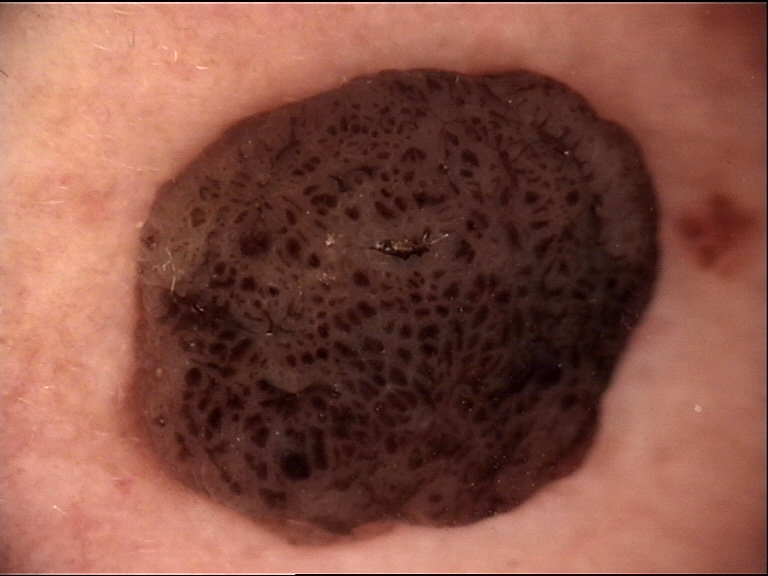A dermoscopic photograph of a skin lesion.
Classified as a banal lesion — a dermal nevus.